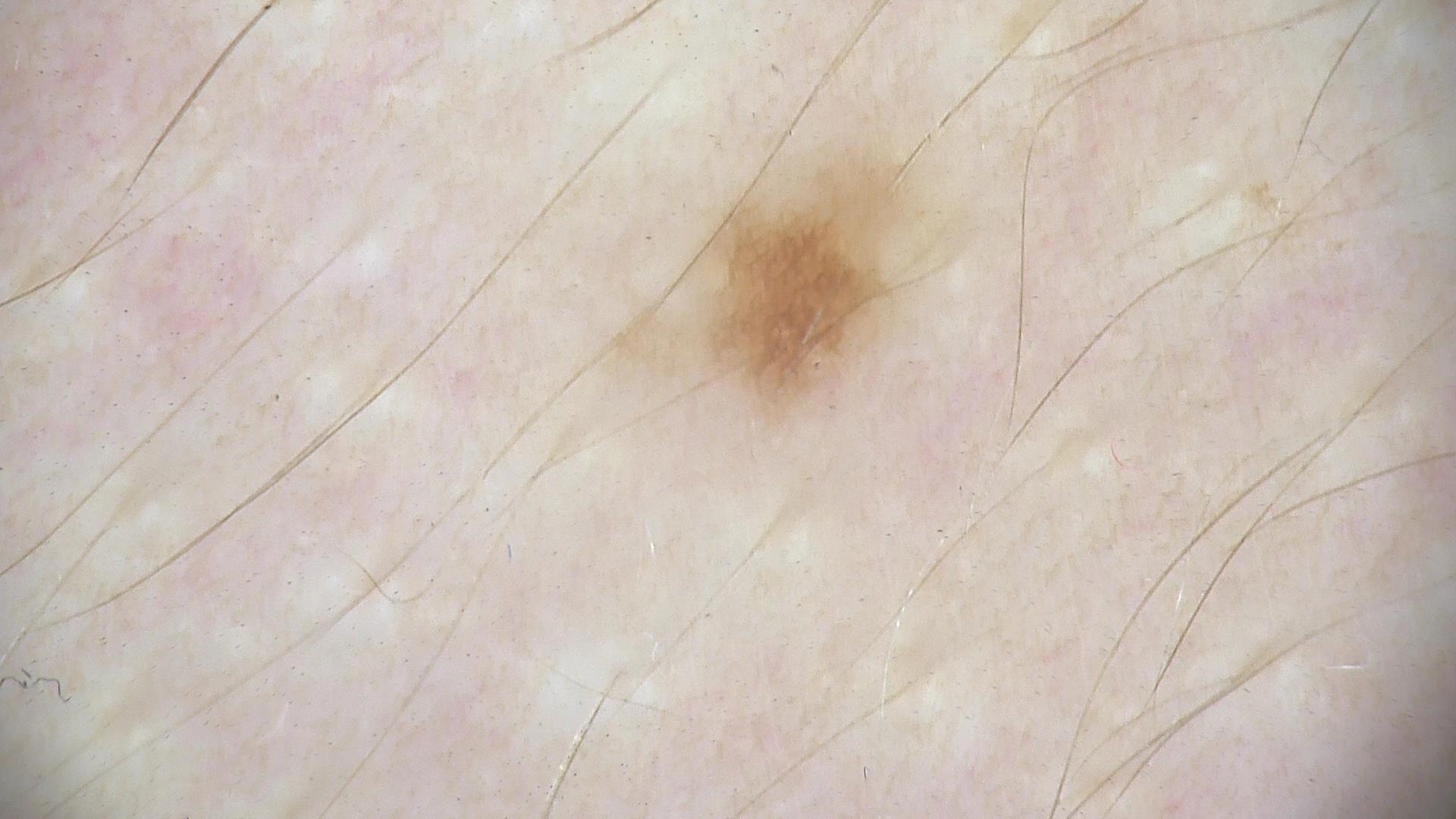imaging: dermoscopy | class: dysplastic junctional nevus (expert consensus).